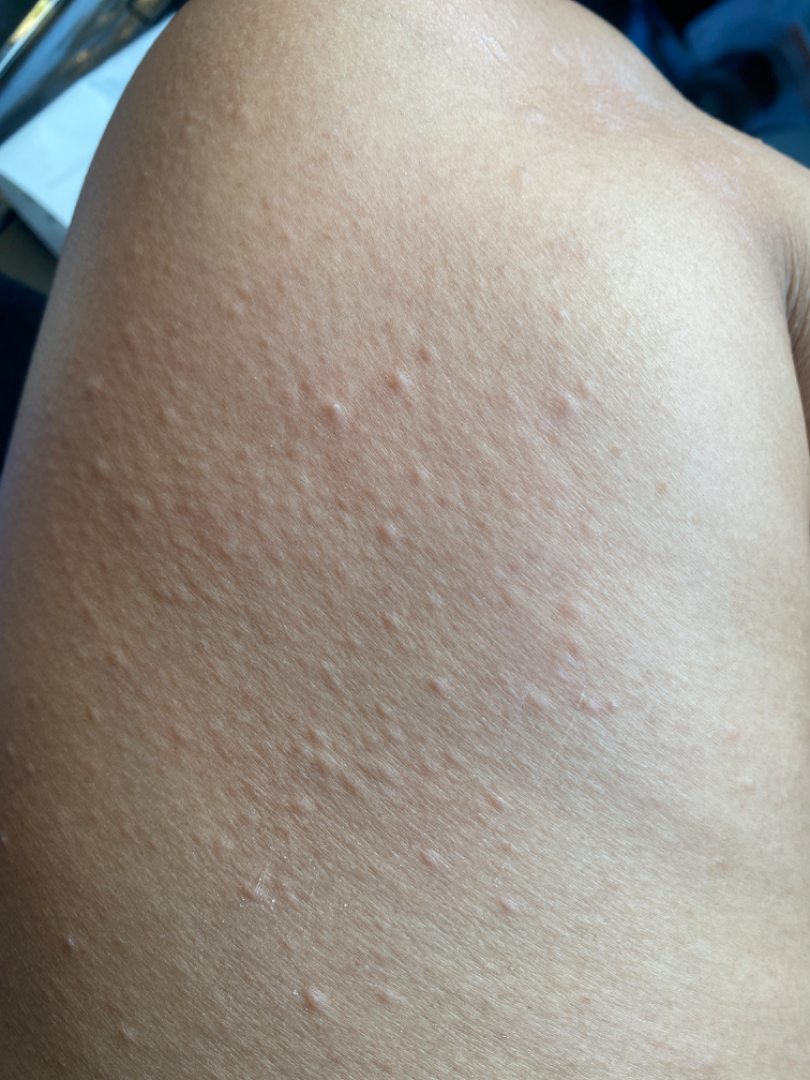Q: What was the assessment?
A: could not be assessed
Q: What is the framing?
A: close-up